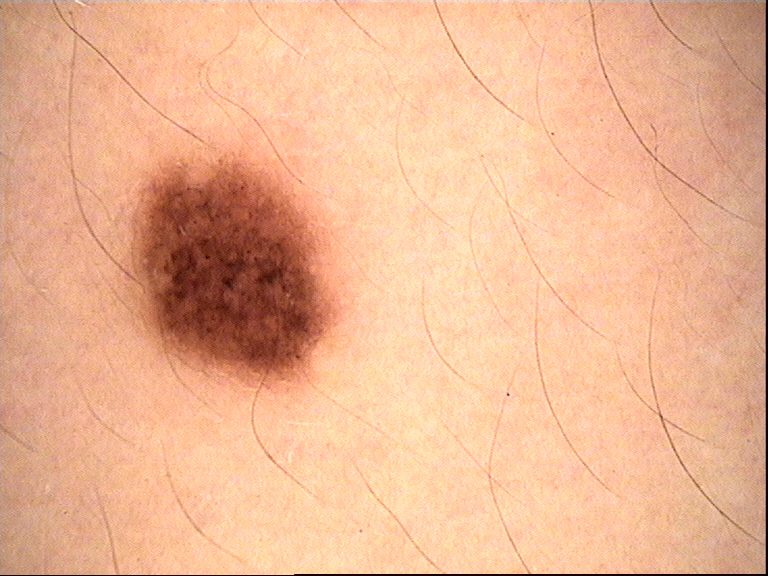Diagnosed as a dysplastic junctional nevus.